The chart notes prior skin cancer (patient or family). A clinical close-up photograph of a skin lesion: 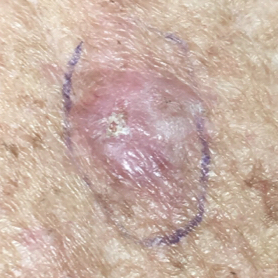body site: the chest | diagnostic label: squamous cell carcinoma (biopsy-proven).